A skin lesion imaged with a dermatoscope.
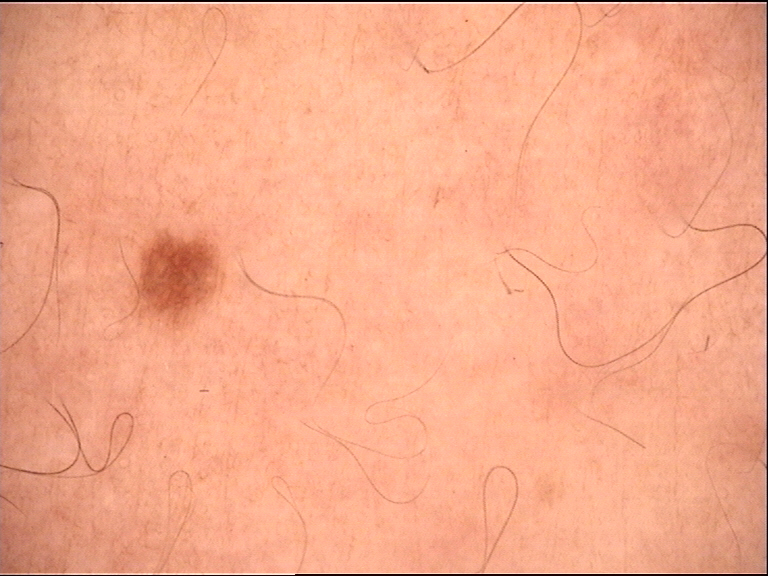The diagnosis was a benign lesion — a dysplastic junctional nevus.